This is a close-up image — 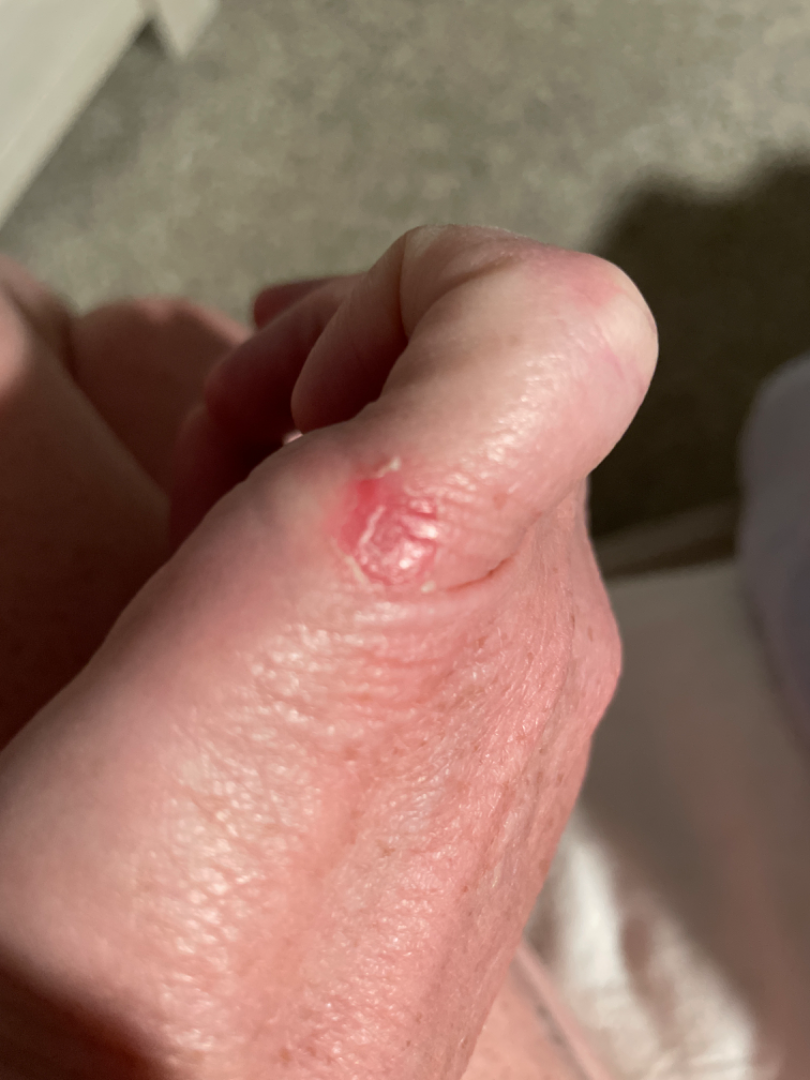Q: What conditions are considered?
A: Eczema (weight 0.55); Skin infection (weight 0.27); Insect Bite (weight 0.18)